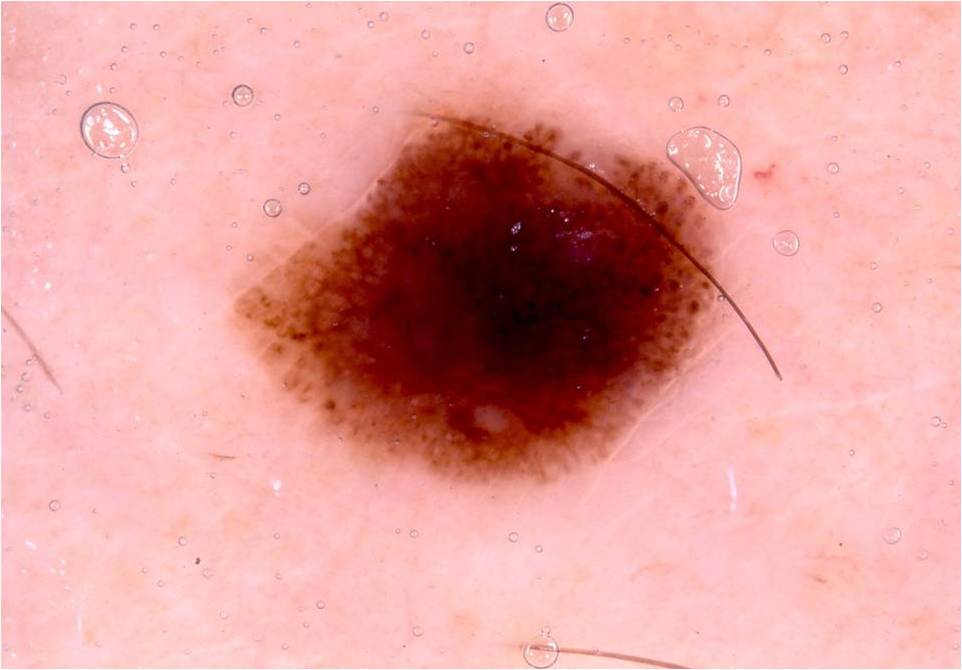A skin lesion imaged with a dermatoscope.
The lesion is located at x1=223 y1=57 x2=735 y2=497.
The lesion was assessed as a benign skin lesion.